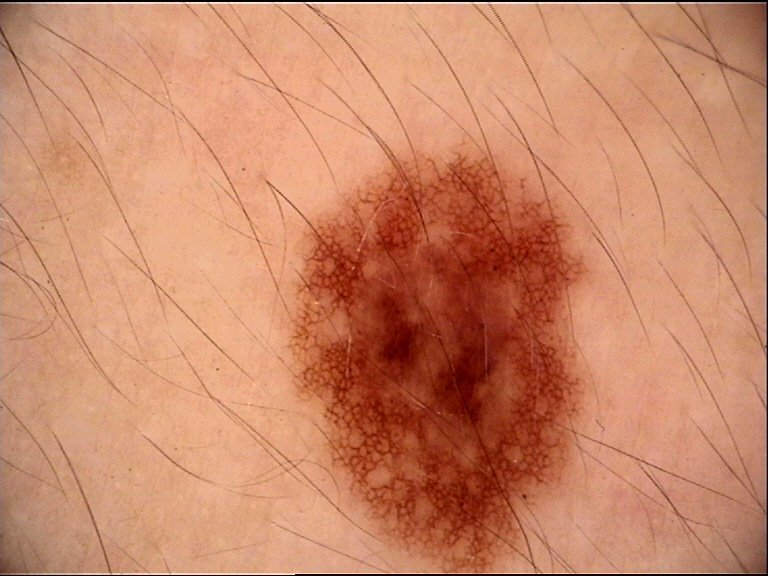Q: What is the imaging modality?
A: dermoscopy
Q: What is this lesion?
A: dysplastic compound nevus (expert consensus)